The affected area is the leg. The subject is 30–39, female. This is a close-up image:
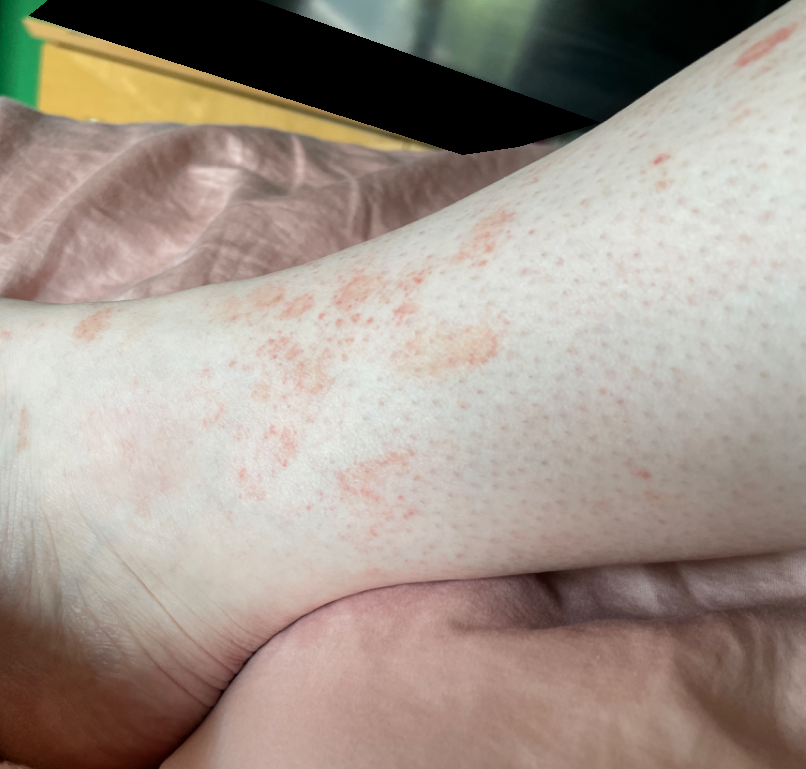Q: What is the dermatologist's impression?
A: in keeping with Pigmented purpuric eruption